The subject is a female aged 30–39 · the photo was captured at a distance · the arm is involved: 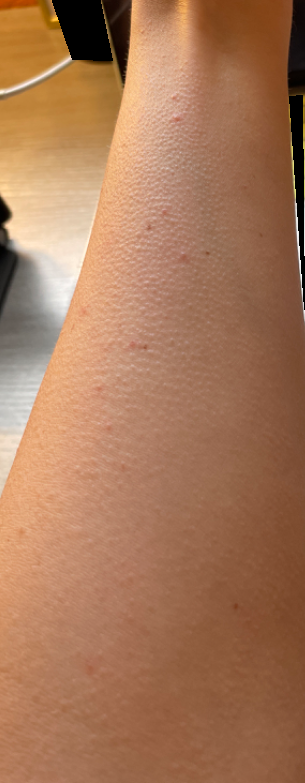Assessment:
The dermatologist could not determine a likely condition from the photograph alone.
Clinical context:
Reported duration is less than one week. The patient described the issue as a rash.